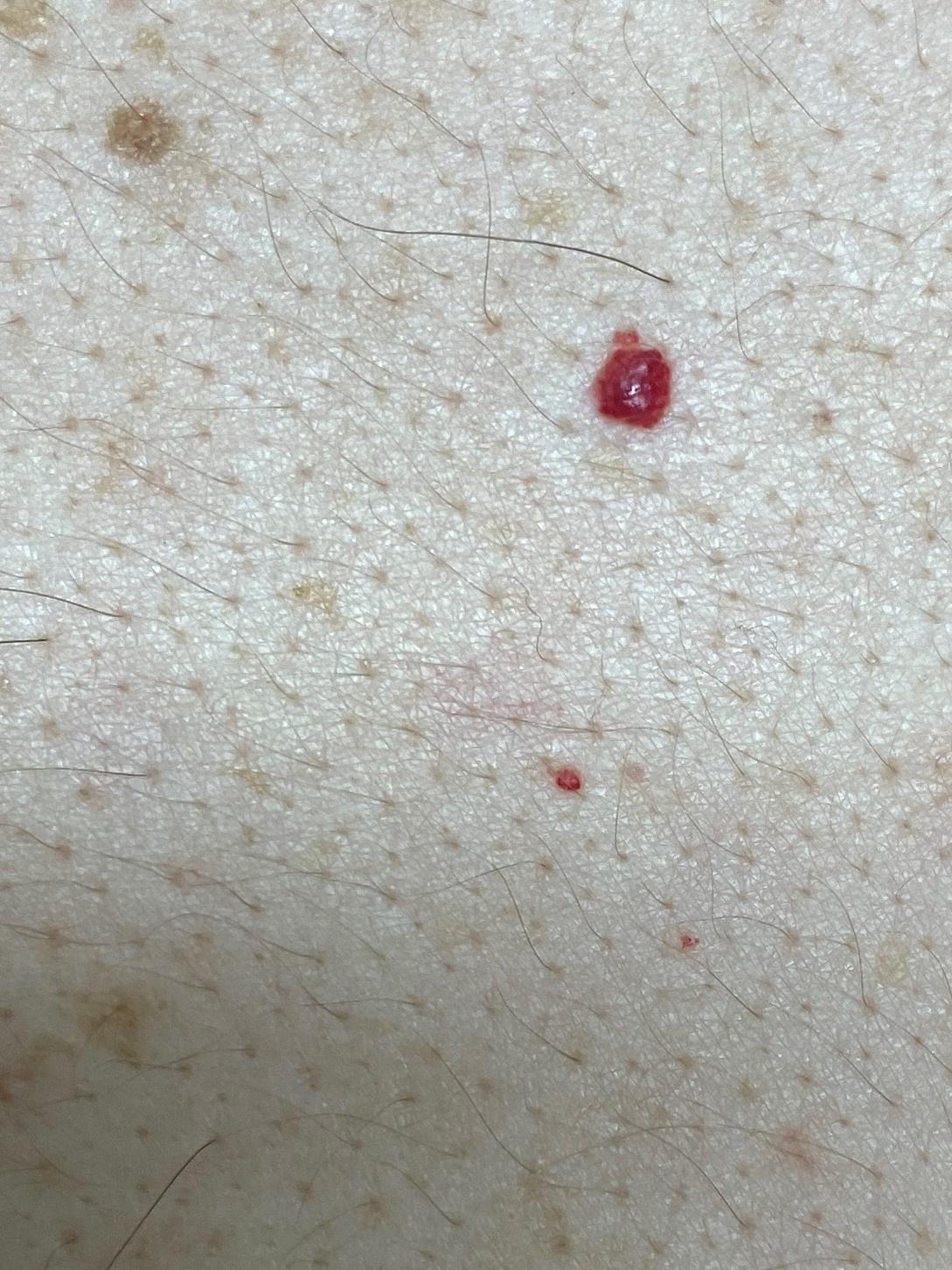Q: Skin phototype?
A: II
Q: What does the history note?
A: a prior melanoma
Q: What are the patient's age and sex?
A: male, aged around 40
Q: Where on the body is the lesion?
A: the trunk
Q: What is the diagnosis?
A: vascular lesion (clinical impression)